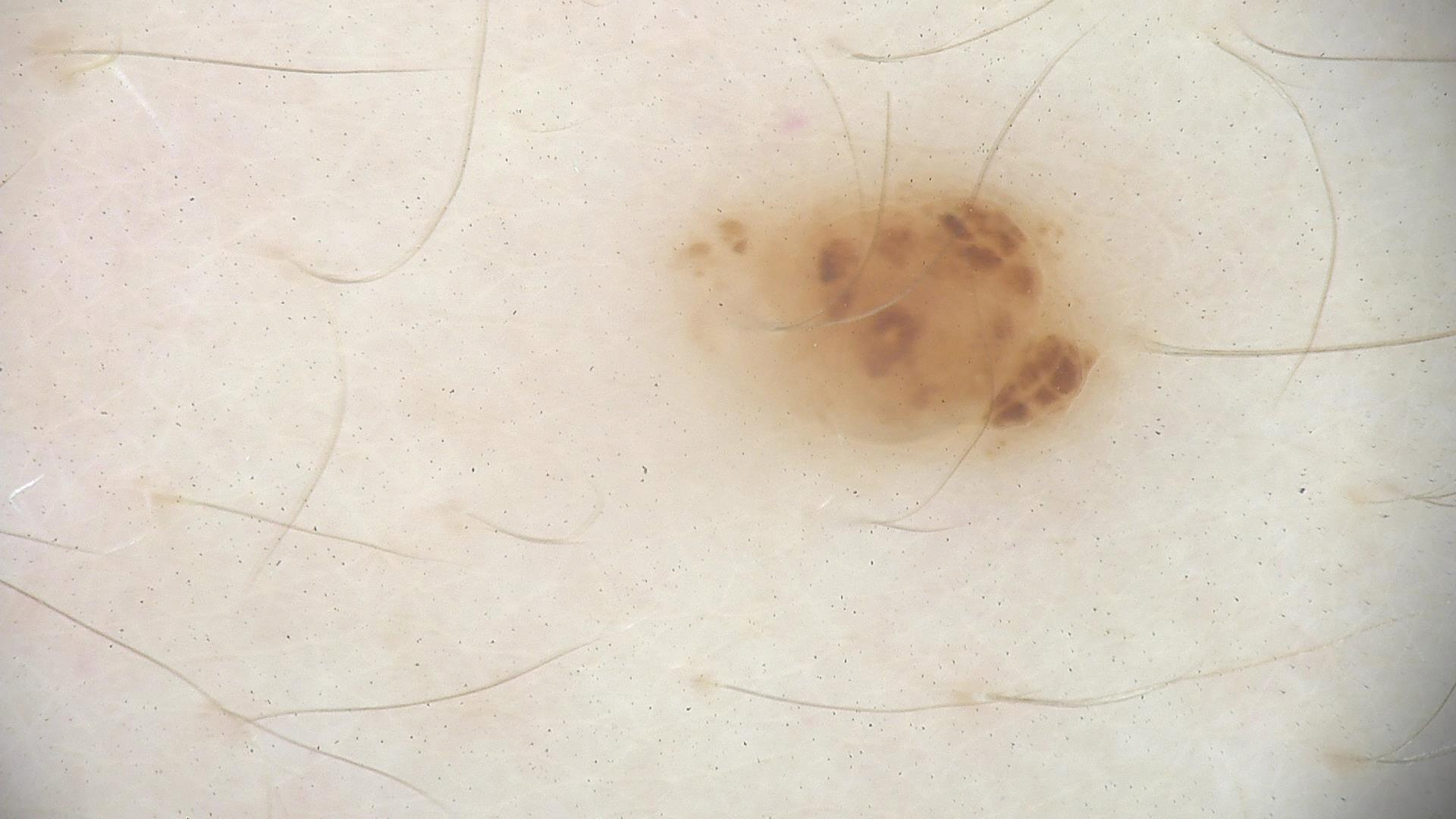The diagnosis was a dysplastic junctional nevus.